Present for one to three months · the lesion involves the front of the torso, arm, leg, head or neck and back of the torso · this is a close-up image · skin tone: Fitzpatrick phototype II.
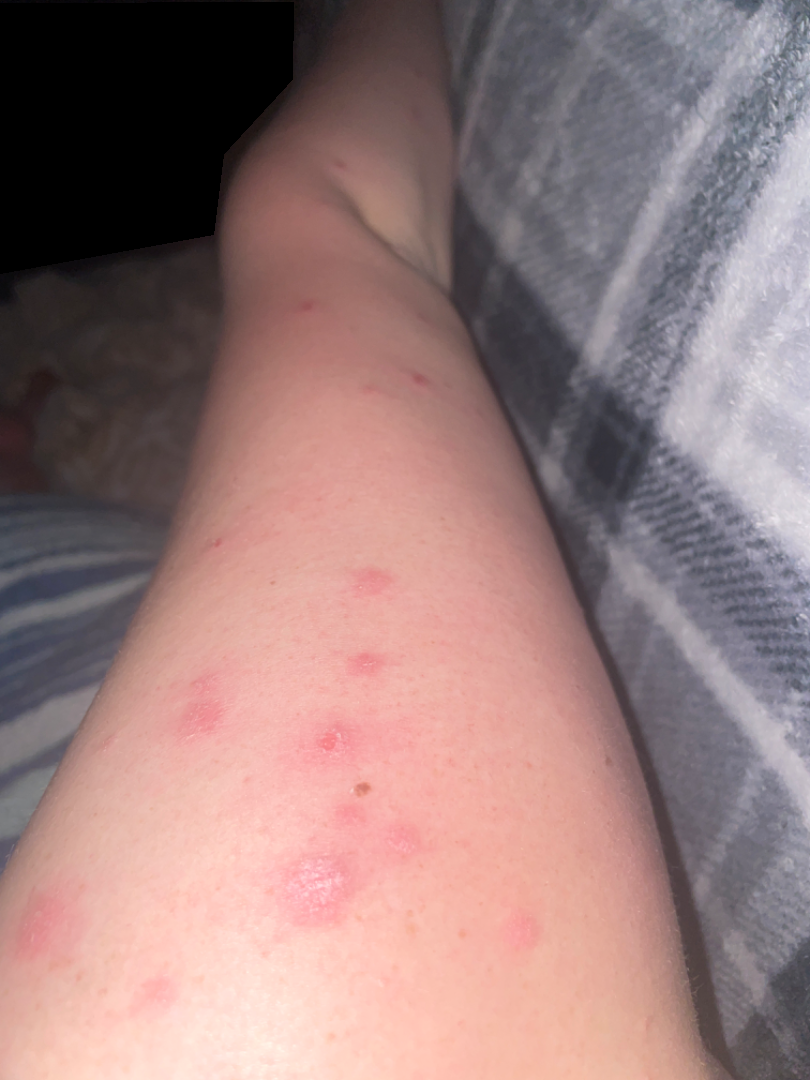• assessment — indeterminate